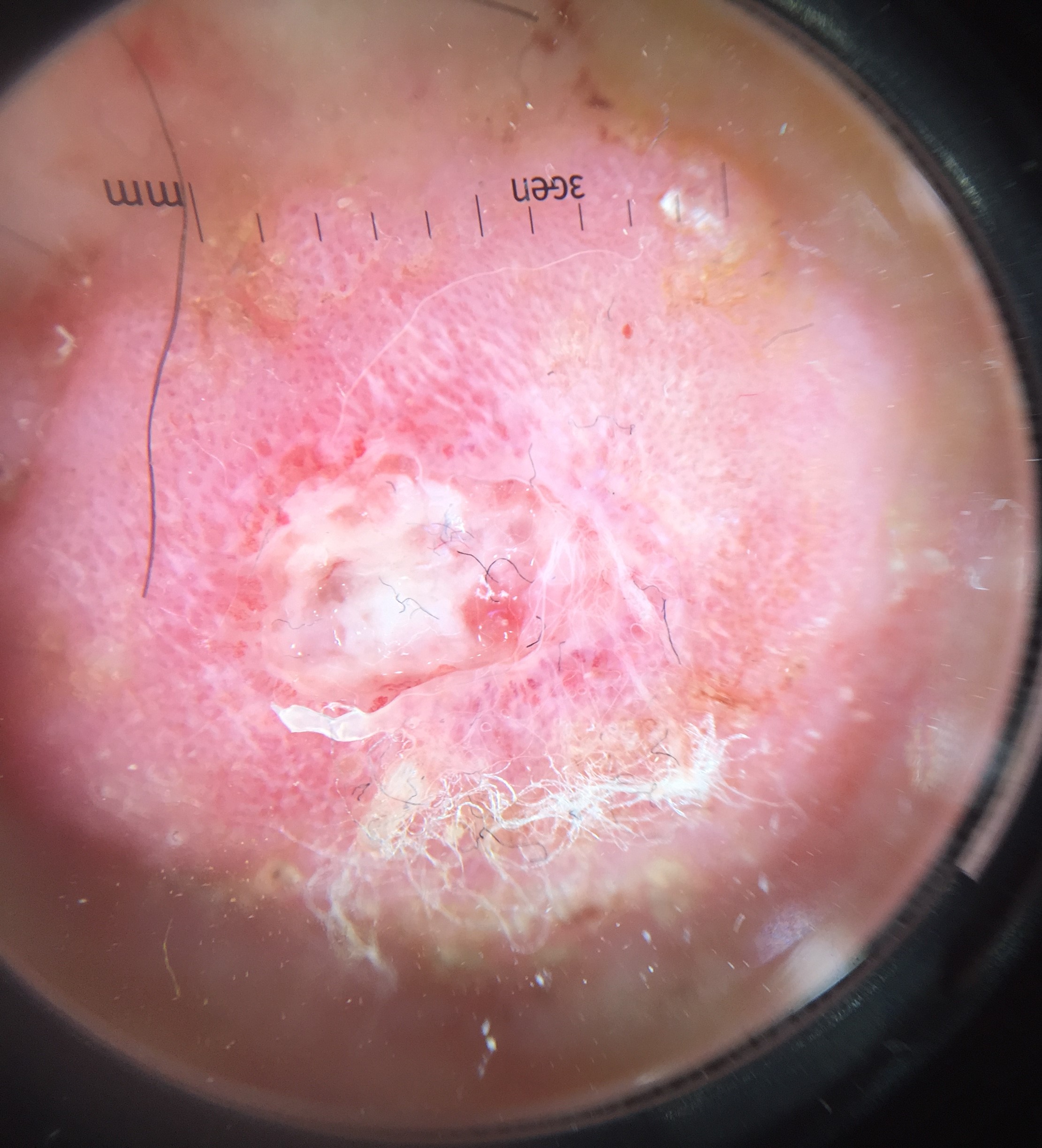image: dermatoscopy
category: keratinocytic
label: squamous cell carcinoma (biopsy-proven)